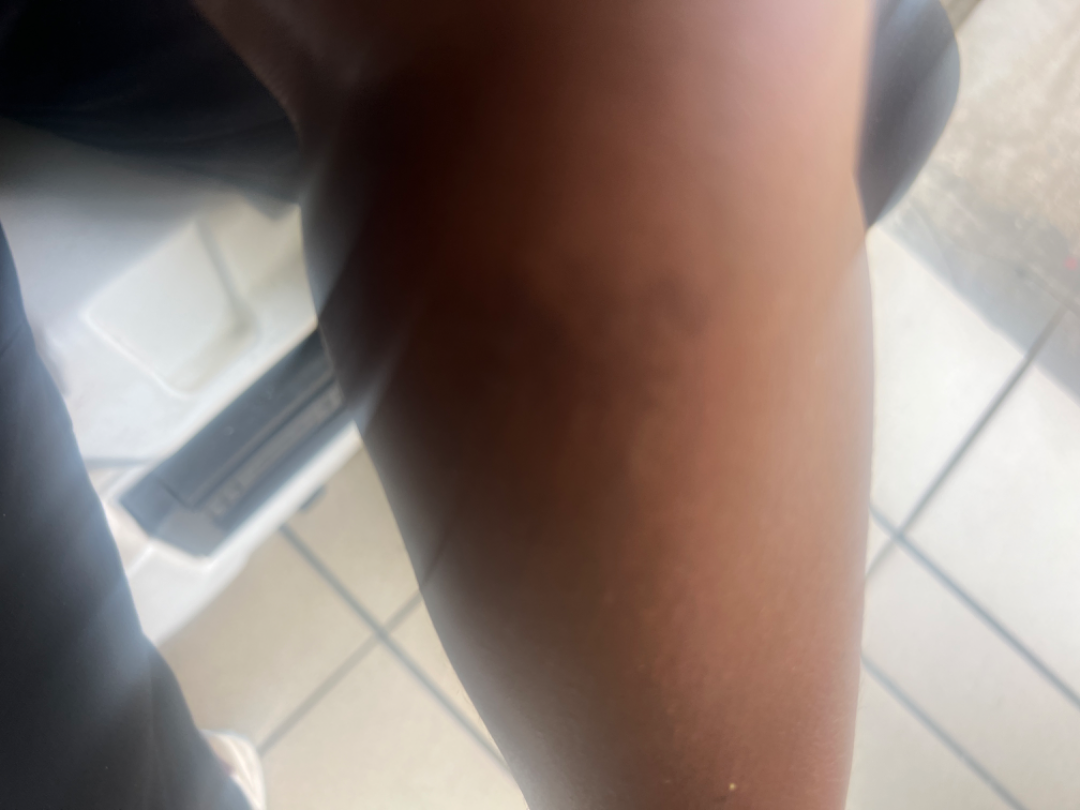assessment = indeterminate | image framing = at an angle.